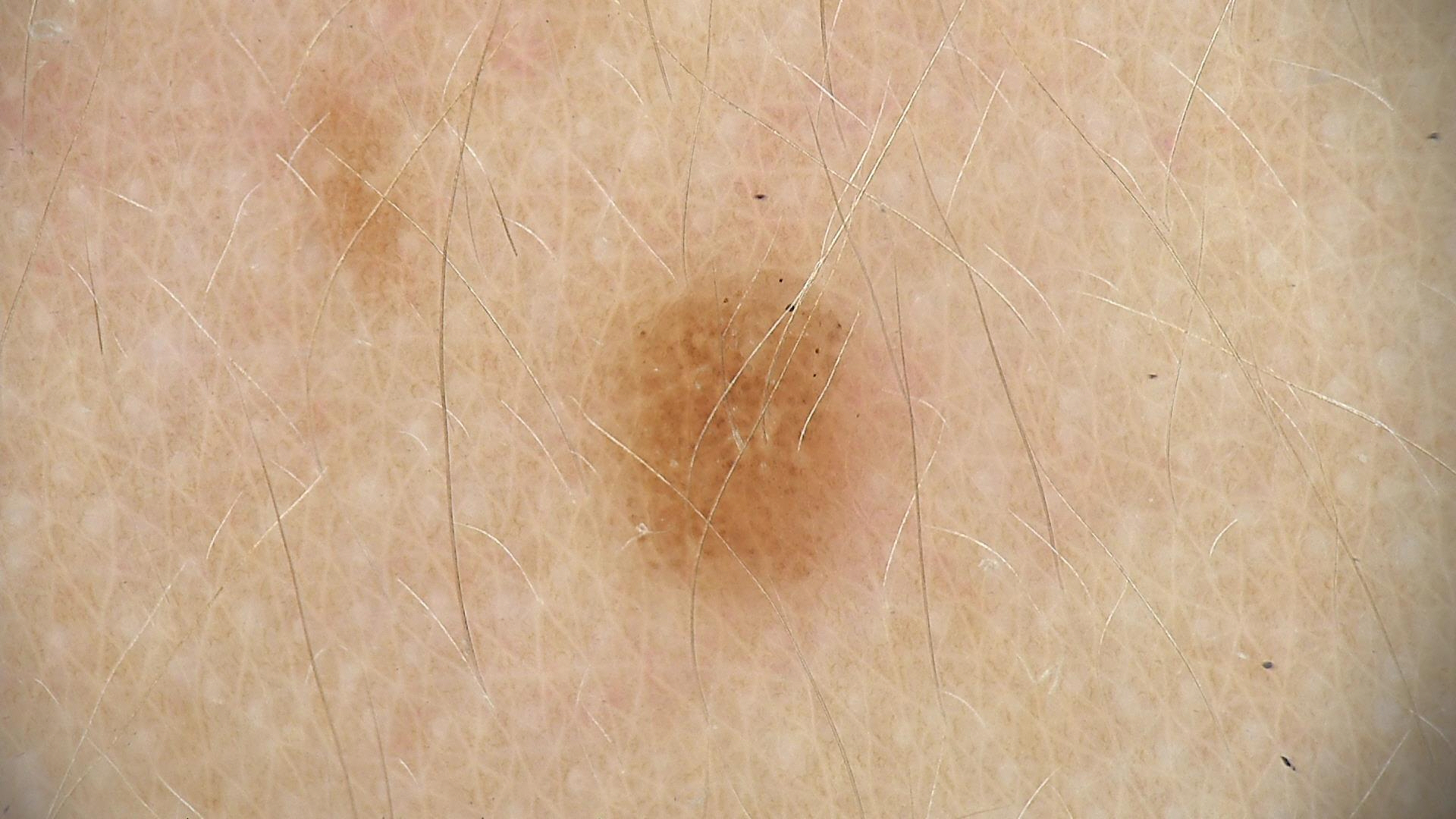class = dysplastic junctional nevus (expert consensus).